The lesion is described as rough or flaky and flat · located on the head or neck · reported lesion symptoms include bothersome appearance · the photo was captured at an angle · the condition has been present for less than one week · the patient is a female aged 18–29:
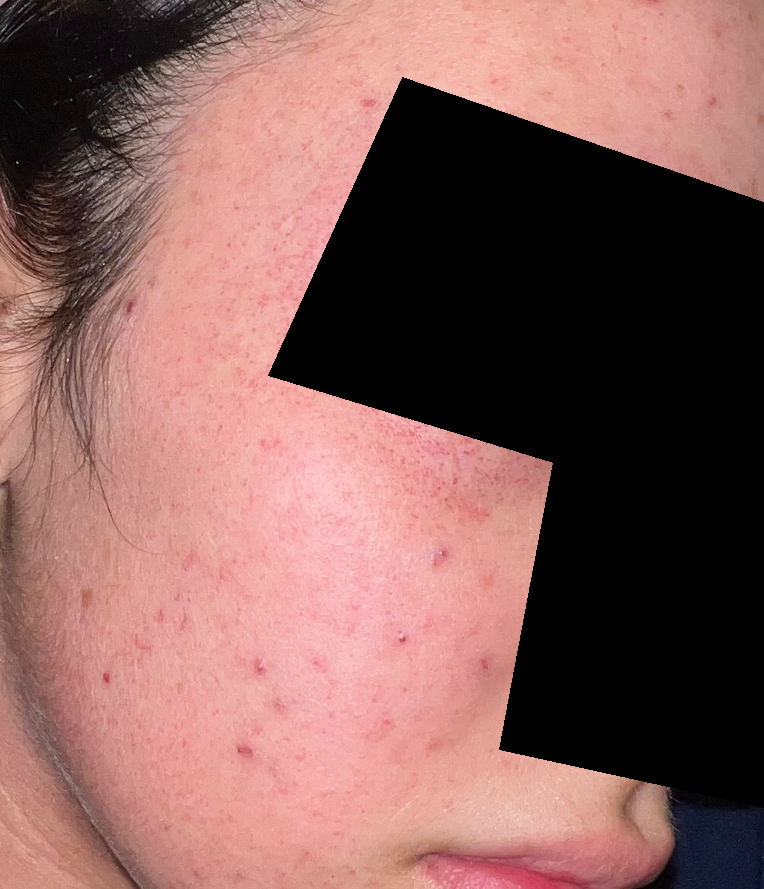Assessment: No differential diagnosis could be assigned on photographic review.